This is a dermoscopic photograph of a skin lesion.
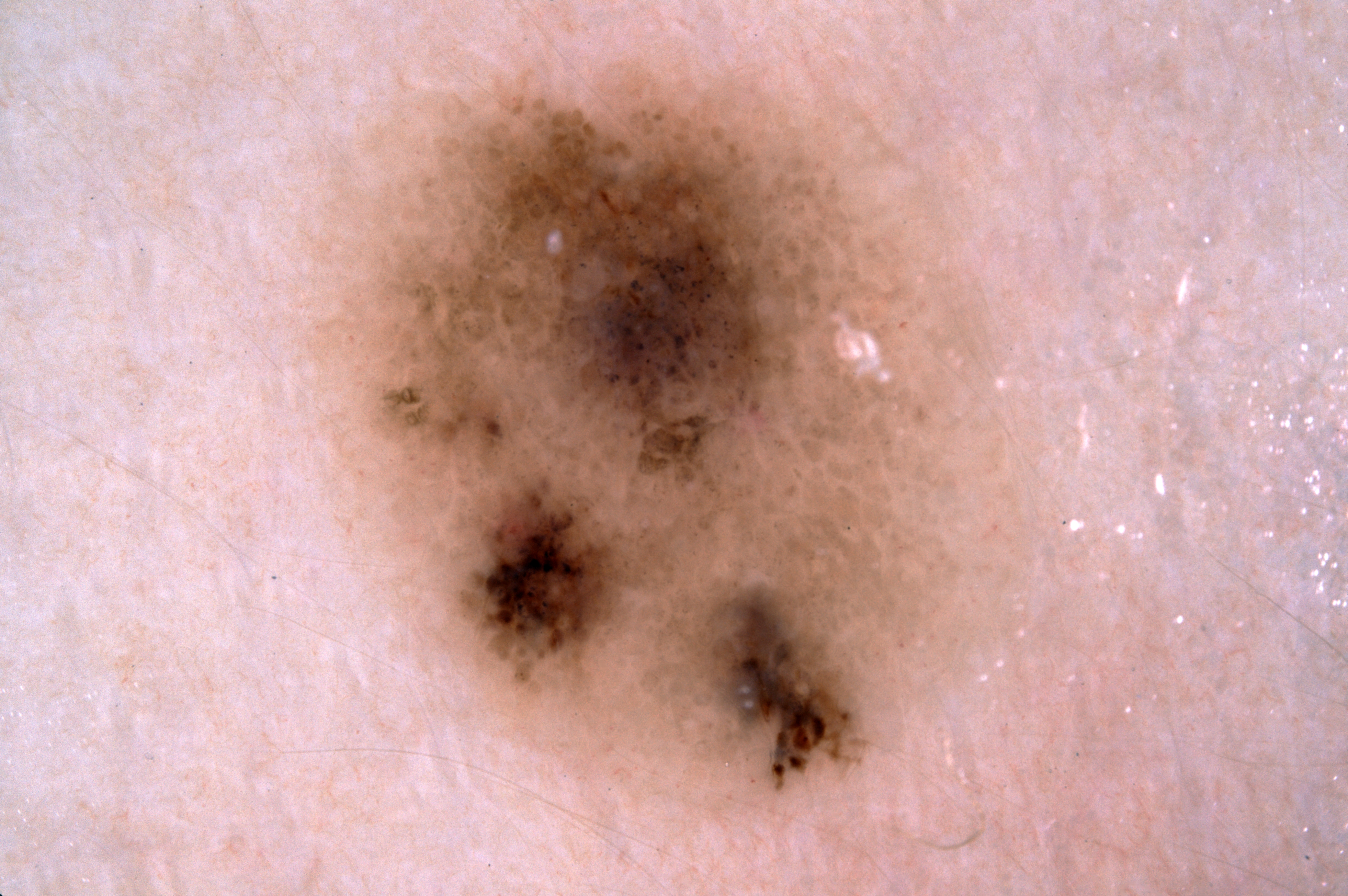As (left, top, right, bottom), the lesion is located at bbox=[316, 63, 1032, 812].
Dermoscopic examination shows negative network.
The diagnostic assessment was a melanocytic nevus.